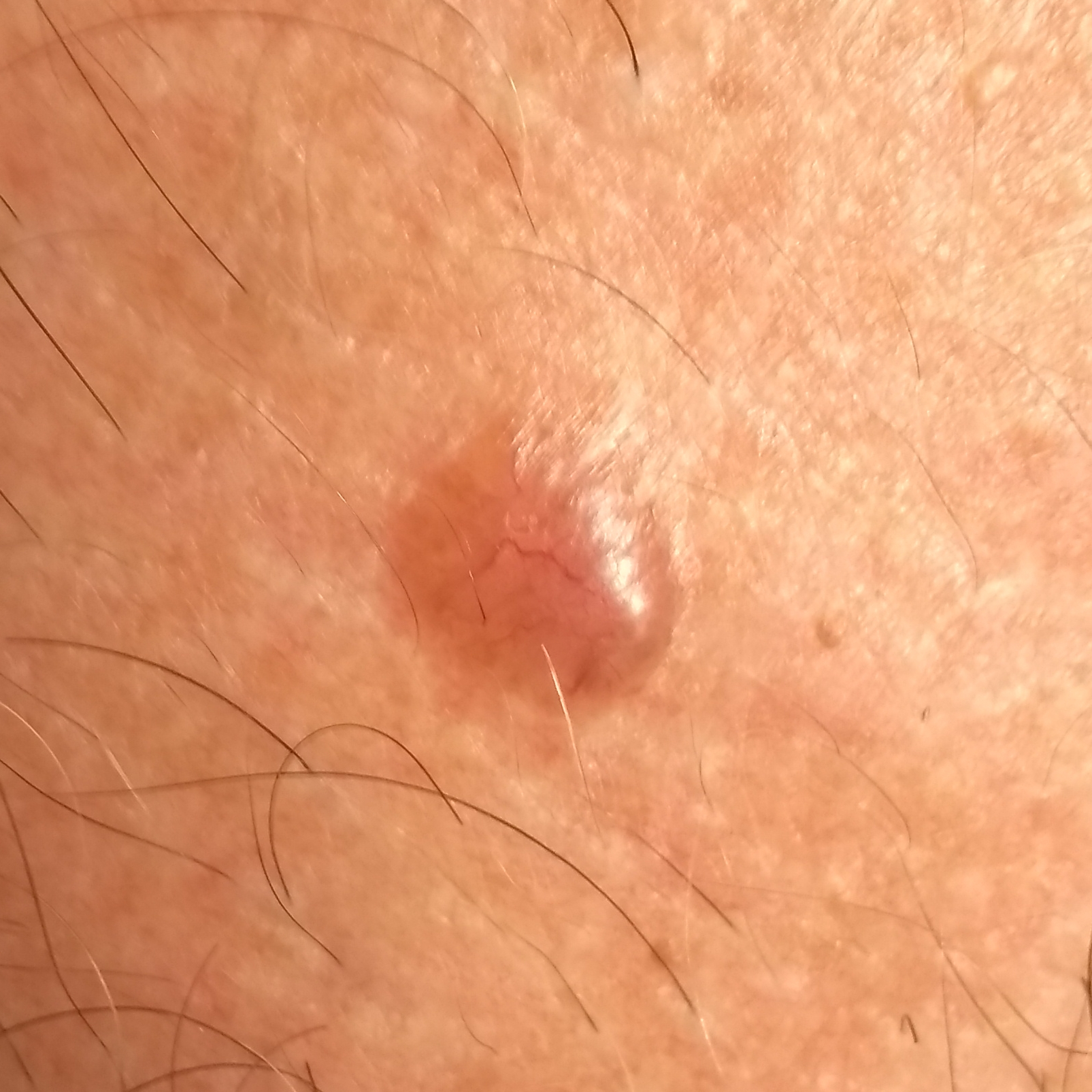On biopsy, the diagnosis was a basal cell carcinoma.